A female patient approximately 35 years of age. A dermoscopic photograph of a skin lesion.
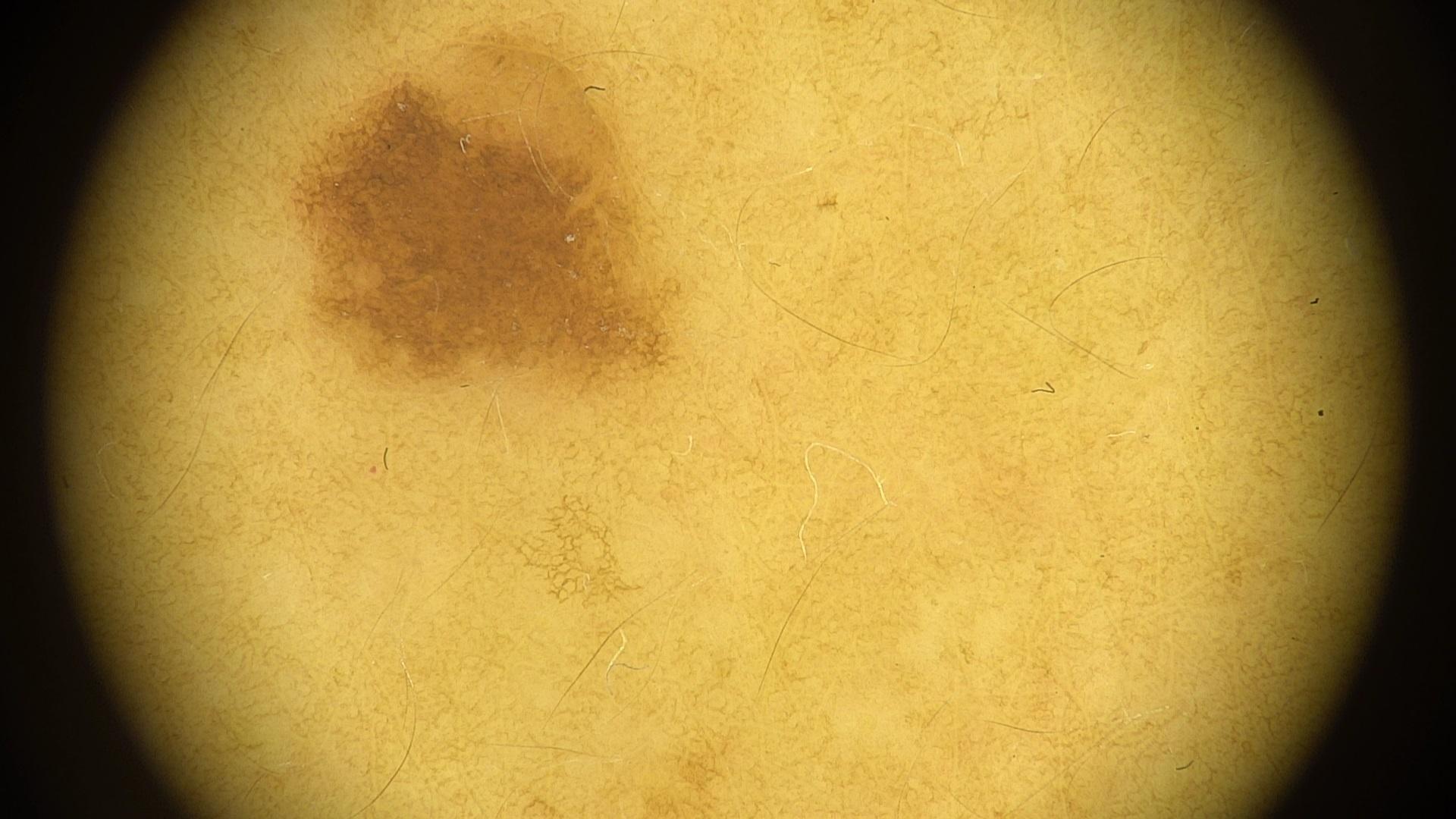The clinical impression was a nevus.